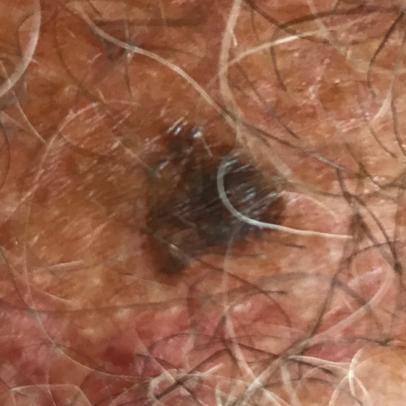Recorded as Fitzpatrick II.
A clinical close-up photograph of a skin lesion.
History notes prior skin cancer (patient or family), pesticide exposure, prior malignancy (patient or family), alcohol use, and no tobacco use.
The lesion measures approximately 10 × 8 mm.
Confirmed on histopathology as a seborrheic keratosis.